The photograph is a close-up of the affected area · the subject is a female aged 30–39 · the lesion involves the front of the torso — 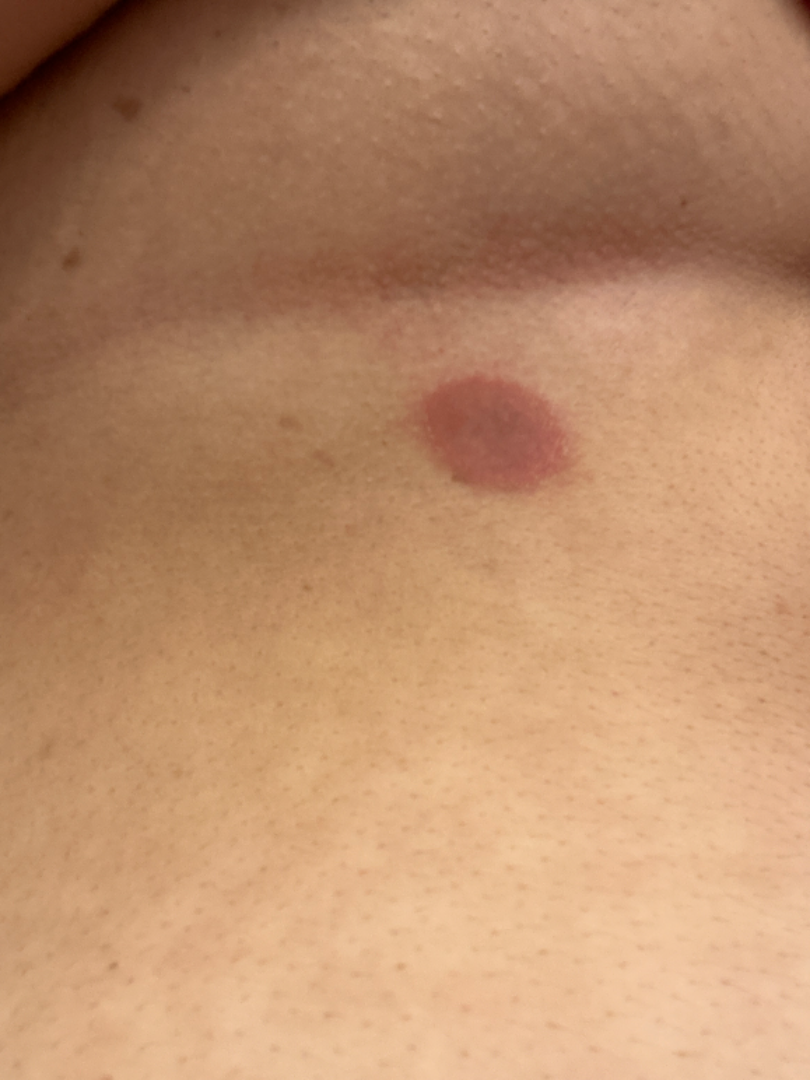assessment: ungradable on photographic review.